History notes alcohol use, prior skin cancer (patient or family), no prior malignancy (patient or family), and no pesticide exposure · recorded as Fitzpatrick I · a clinical close-up photograph of a skin lesion: 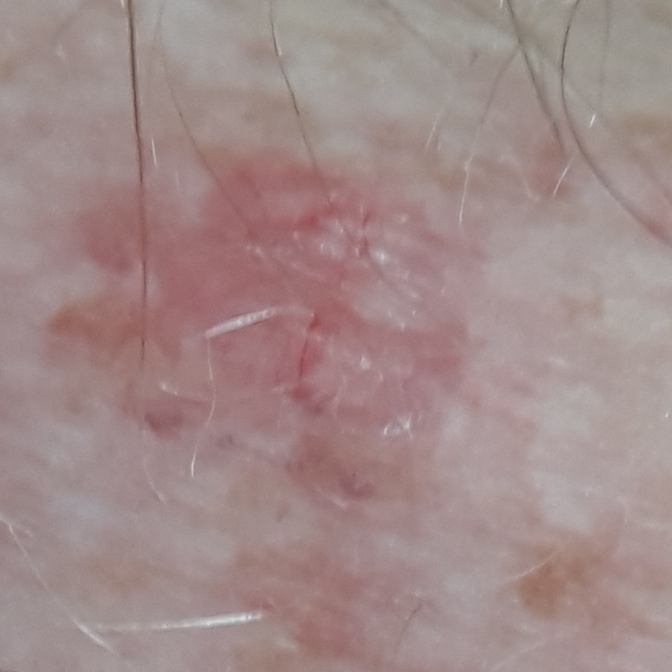Case summary:
The lesion is on a forearm. The lesion measures 5 × 5 mm. The patient reports that the lesion has bled, is elevated, itches, and has grown.
Conclusion:
Histopathology confirmed a basal cell carcinoma.